An image taken at an angle · the leg is involved:
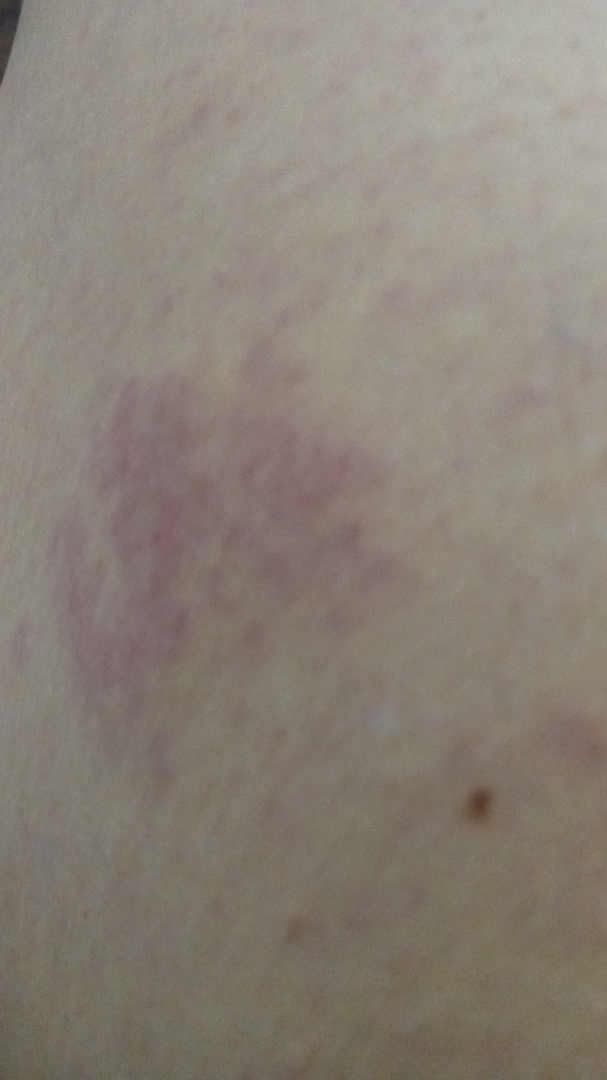{"assessment": "unable to determine", "texture": "raised or bumpy", "patient_category": "a rash", "duration": "about one day"}